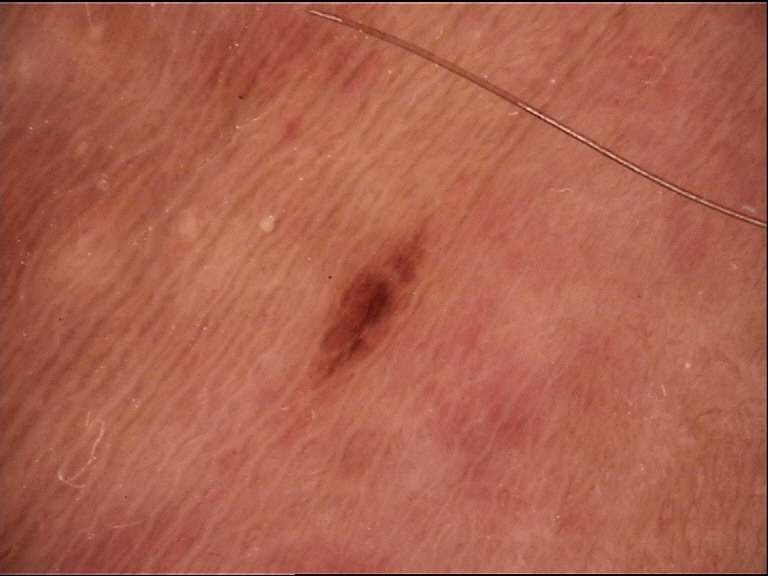Summary:
This is a banal lesion.
Conclusion:
Classified as a junctional nevus.